A dermoscopic image of a skin lesion.
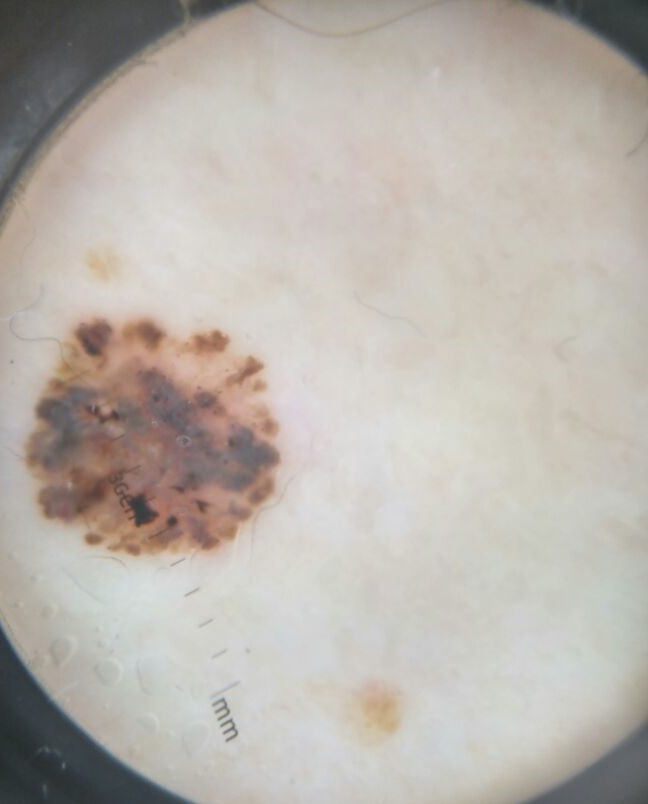Findings: This is a keratinocytic lesion. Pathology: The biopsy diagnosis was a basal cell carcinoma.